The lesion is described as raised or bumpy. The patient is a female aged 60–69. Close-up view. The patient did not report lesion symptoms. Located on the arm. Self-reported Fitzpatrick skin type III. No constitutional symptoms were reported: 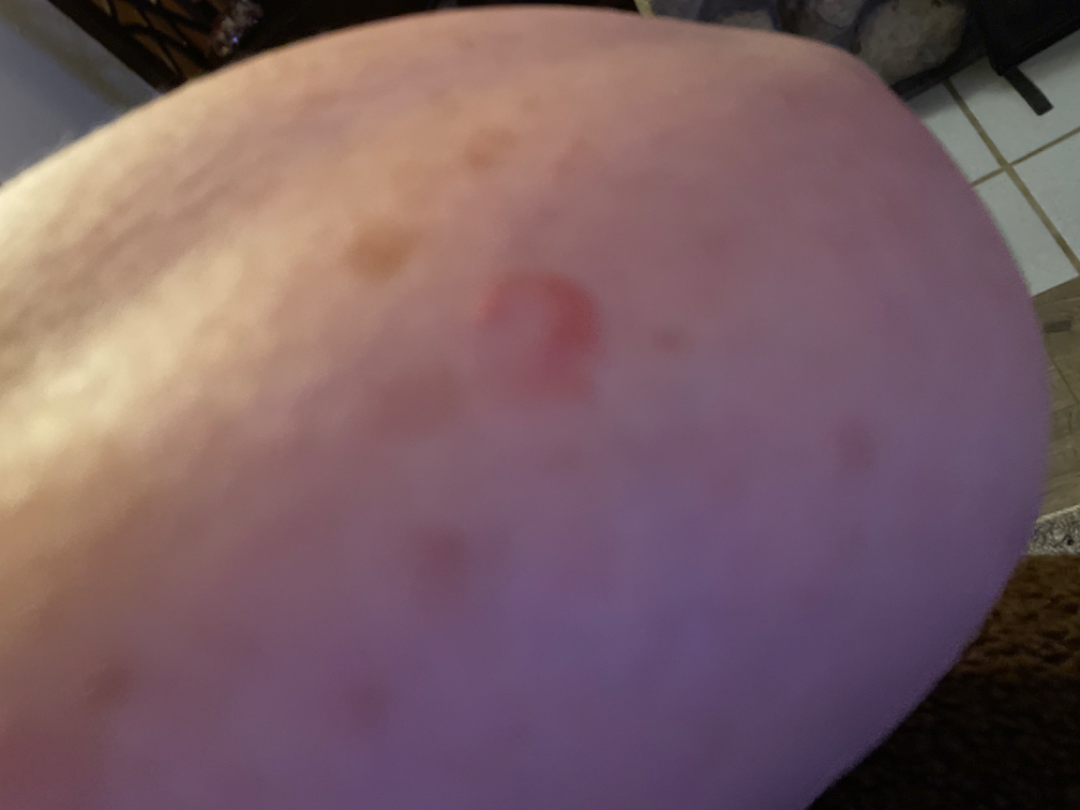Q: What was the assessment?
A: unable to determine